The lesion involves the arm; a close-up photograph; reported lesion symptoms include burning and itching; the contributor reports the lesion is raised or bumpy; the contributor reports the condition has been present for less than one week; self-categorized by the patient as a rash: 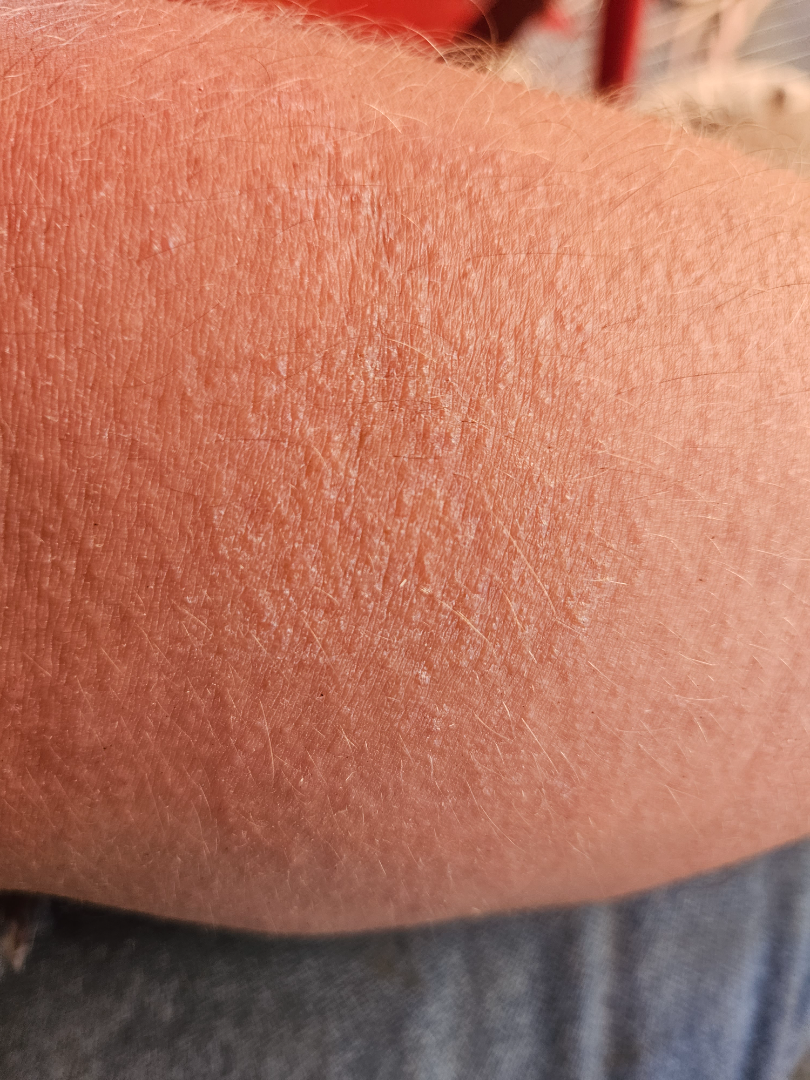On teledermatology review: Allergic Contact Dermatitis (possible); Xerosis (possible); Eczema (possible); Sunburn (lower probability); Keratosis pilaris (lower probability).